The photograph is a close-up of the affected area.
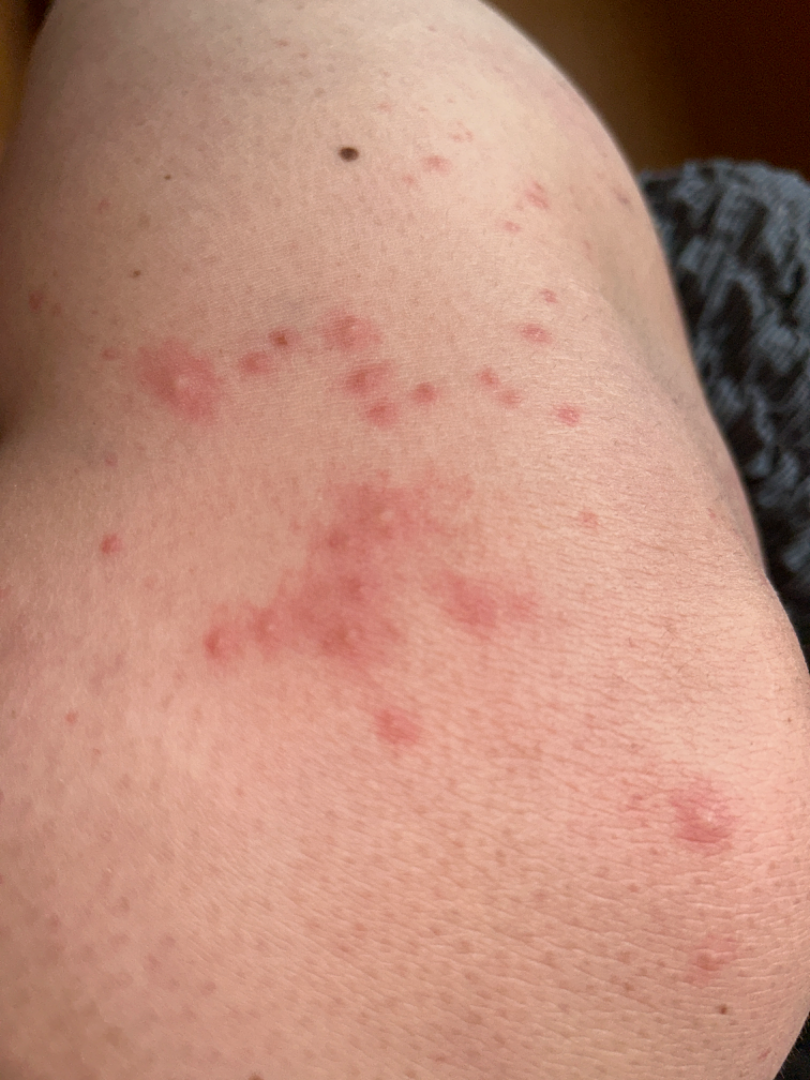assessment = could not be assessed.